A dermoscopy image of a single skin lesion.
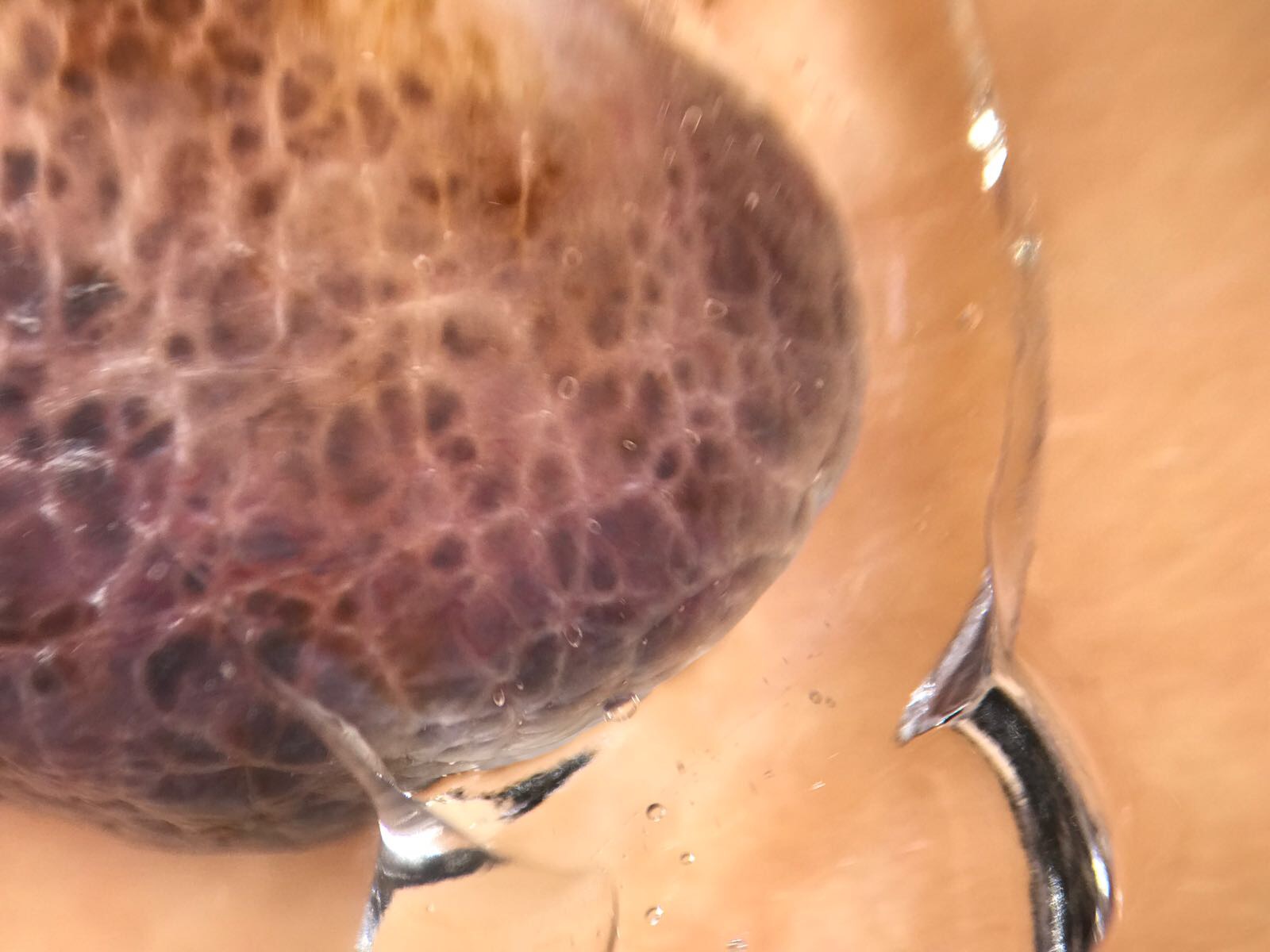Conclusion: Confirmed on histopathology as a melanoma.